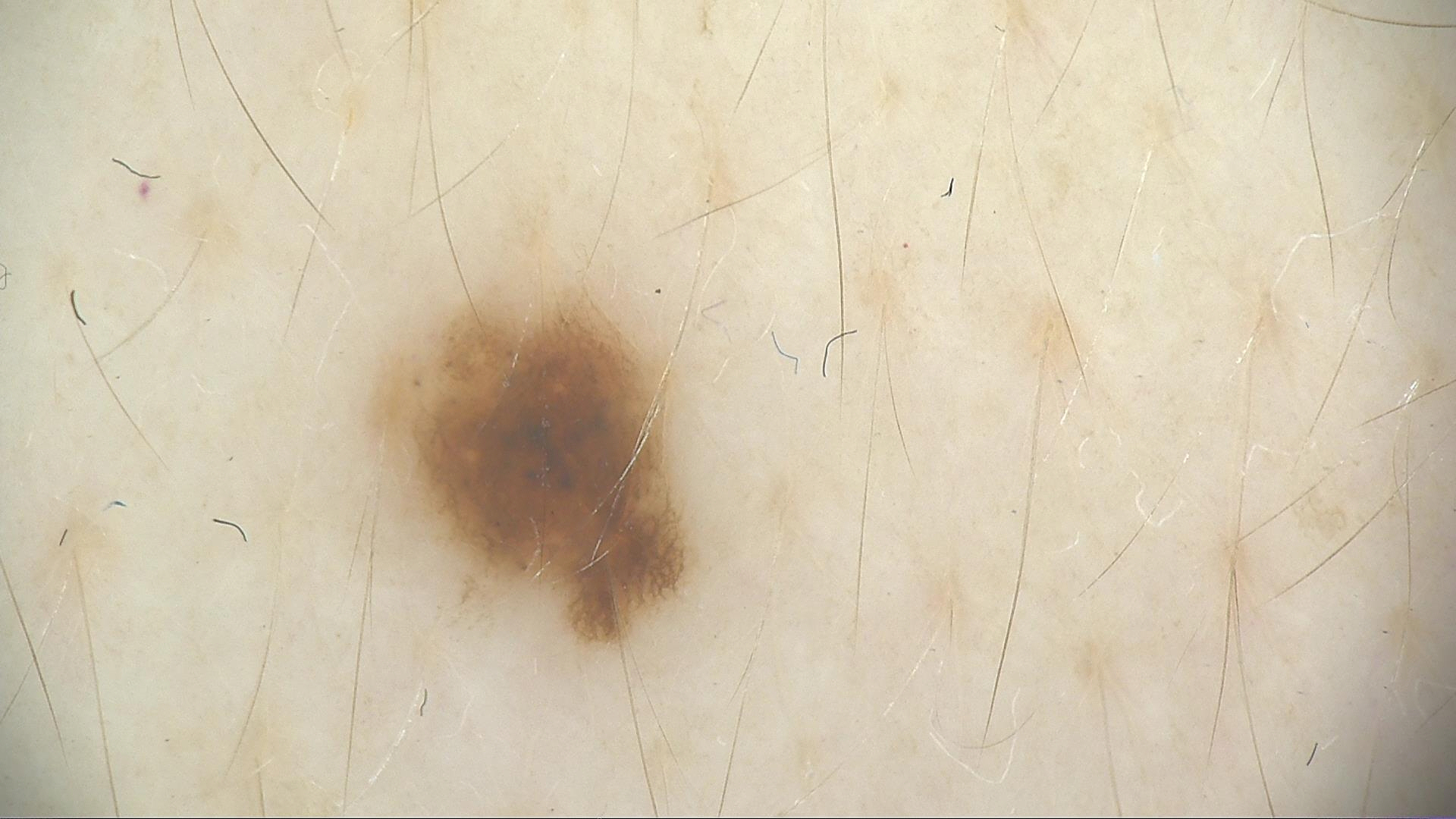The diagnosis was a dysplastic junctional nevus.